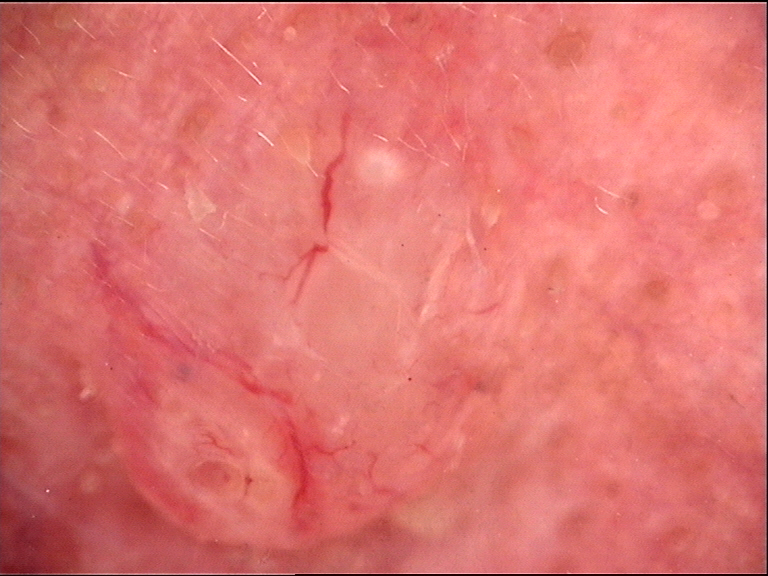label = basal cell carcinoma (biopsy-proven).